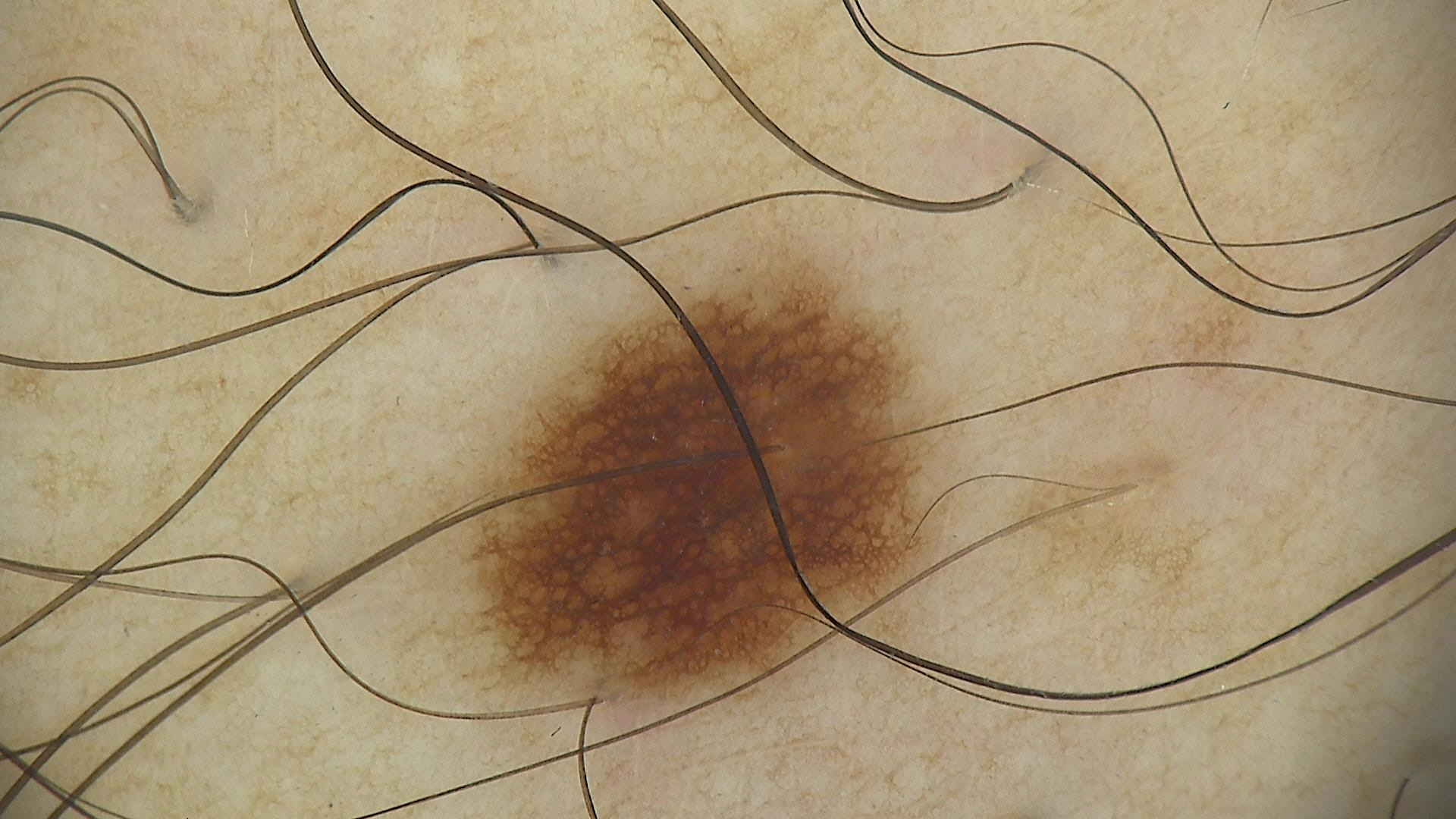| key | value |
|---|---|
| label | dysplastic junctional nevus (expert consensus) |